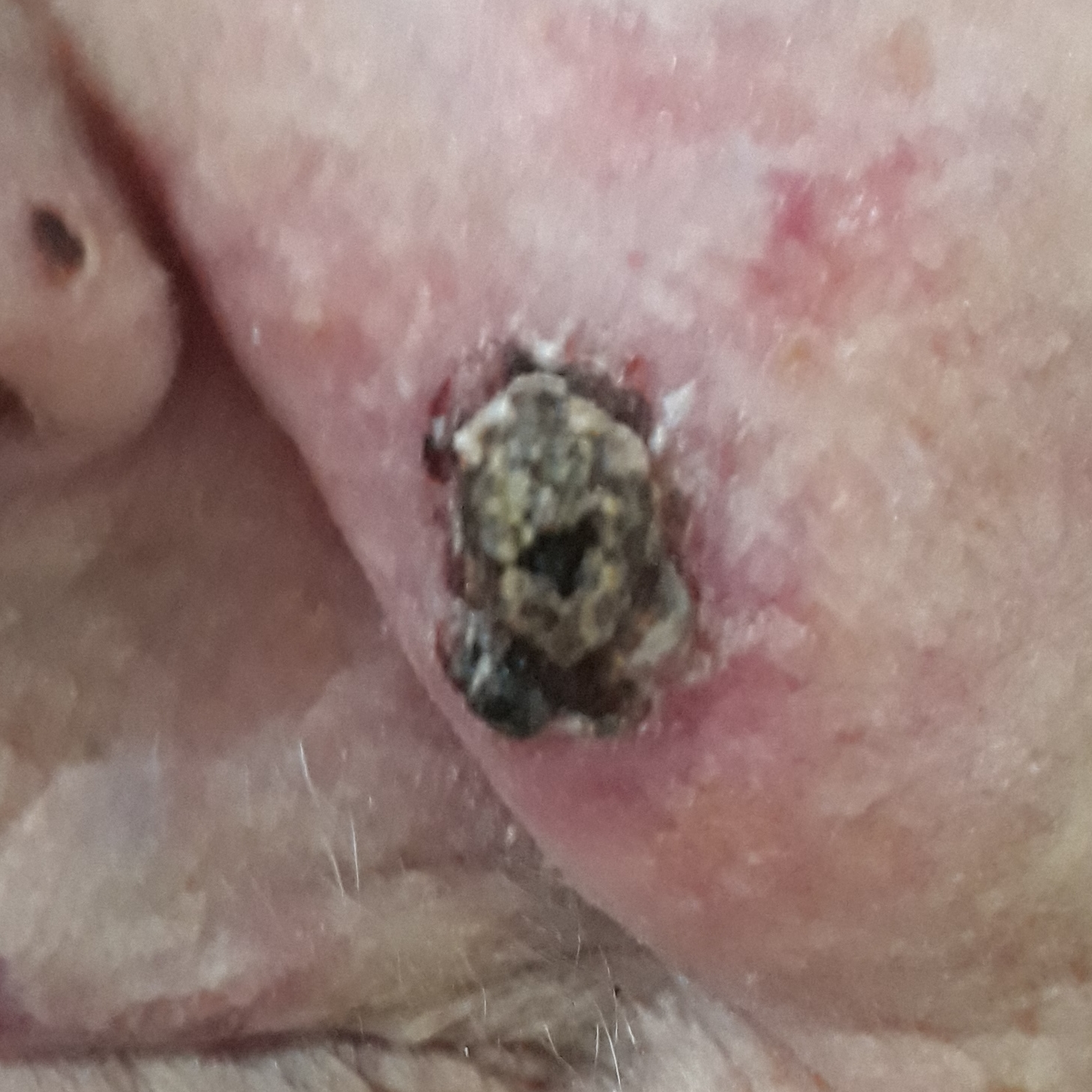Summary: A female patient in their 90s. A clinical photograph showing a skin lesion. Recorded as Fitzpatrick phototype II. The lesion was found on the face. Measuring about 15 × 8 mm. Per patient report, the lesion is elevated, hurts, itches, has bled, has changed, and has grown. Diagnosis: Histopathological examination showed a skin cancer — a basal cell carcinoma.